A skin lesion imaged with a dermatoscope.
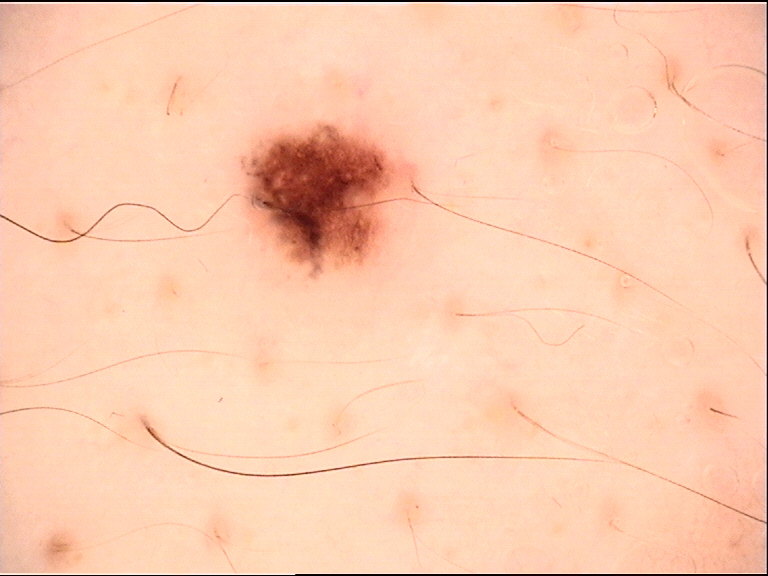Labeled as a benign lesion — a dysplastic junctional nevus.